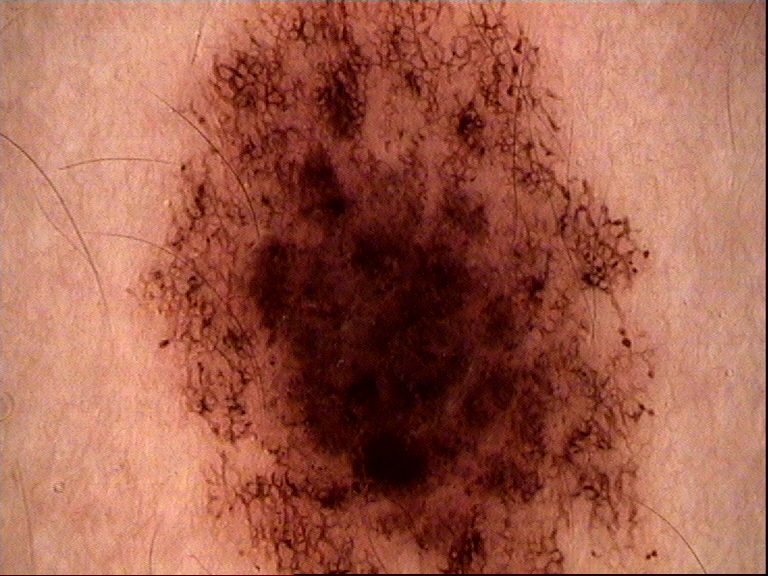{"diagnosis": {"name": "dysplastic compound nevus", "code": "cd", "malignancy": "benign", "super_class": "melanocytic", "confirmation": "expert consensus"}}